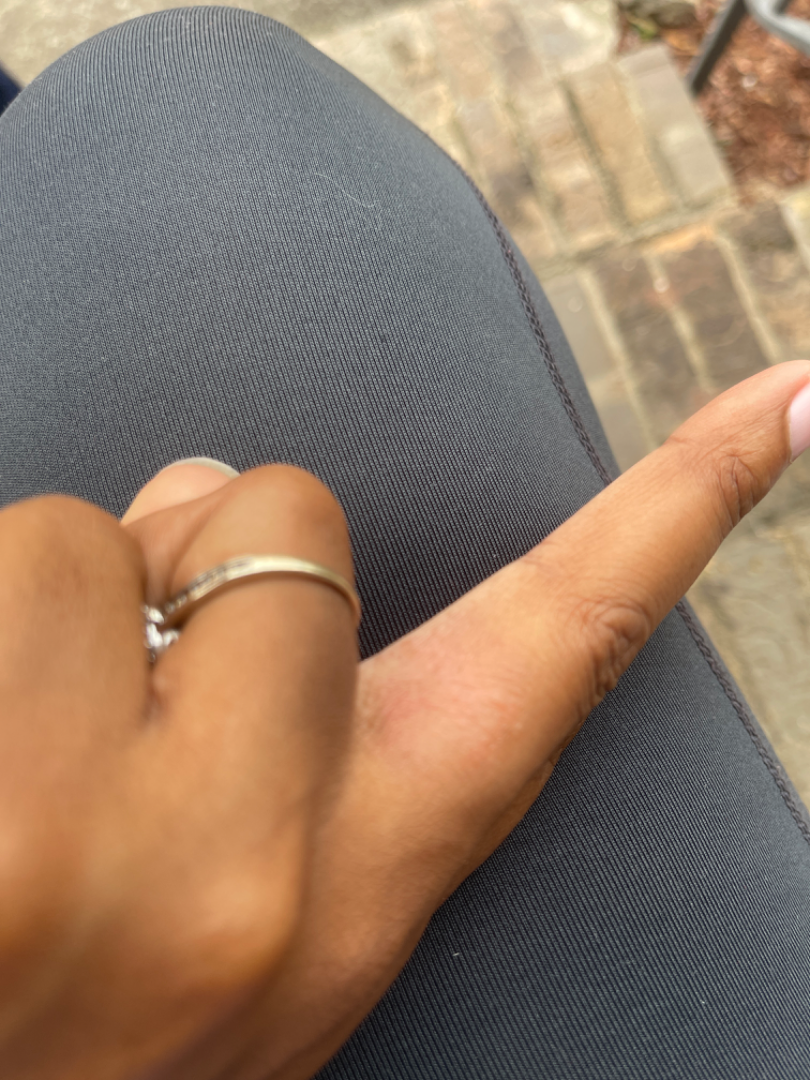Case summary:
- assessment: indeterminate from the photograph
- image framing: close-up
- anatomic site: back of the hand